A female subject, aged 13 to 17. A skin lesion imaged with a dermatoscope:
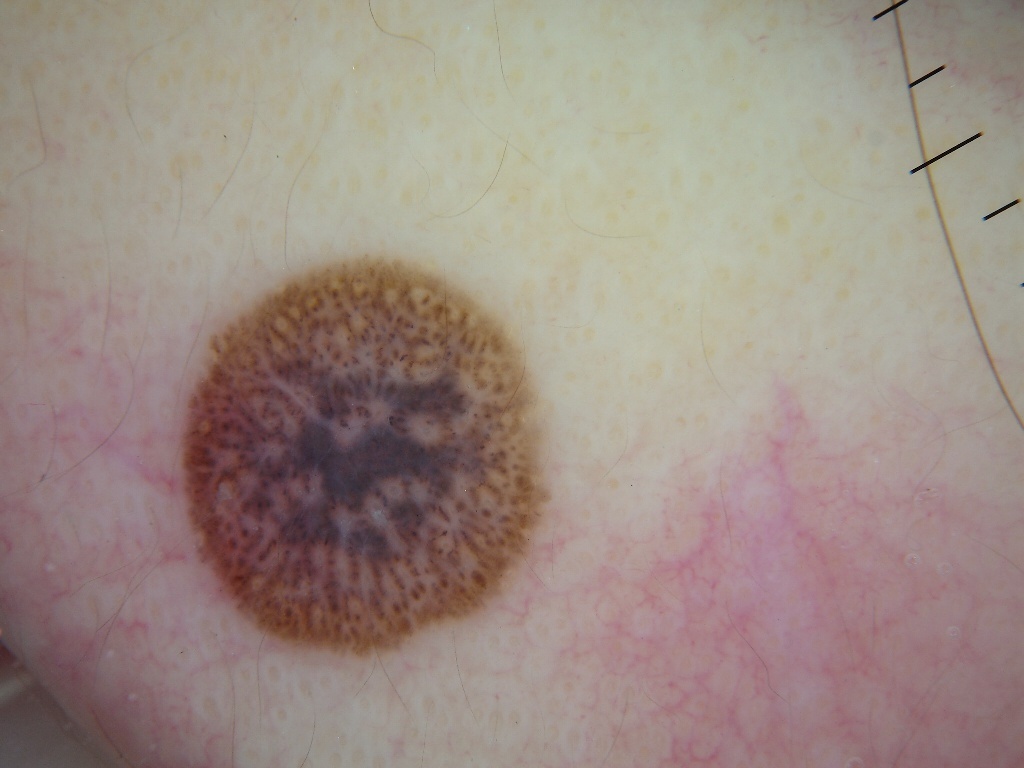• dermoscopic findings — globules; absent: negative network, streaks, milia-like cysts, and pigment network
• location — 175, 250, 558, 668
• diagnostic label — a melanocytic nevus, a benign lesion